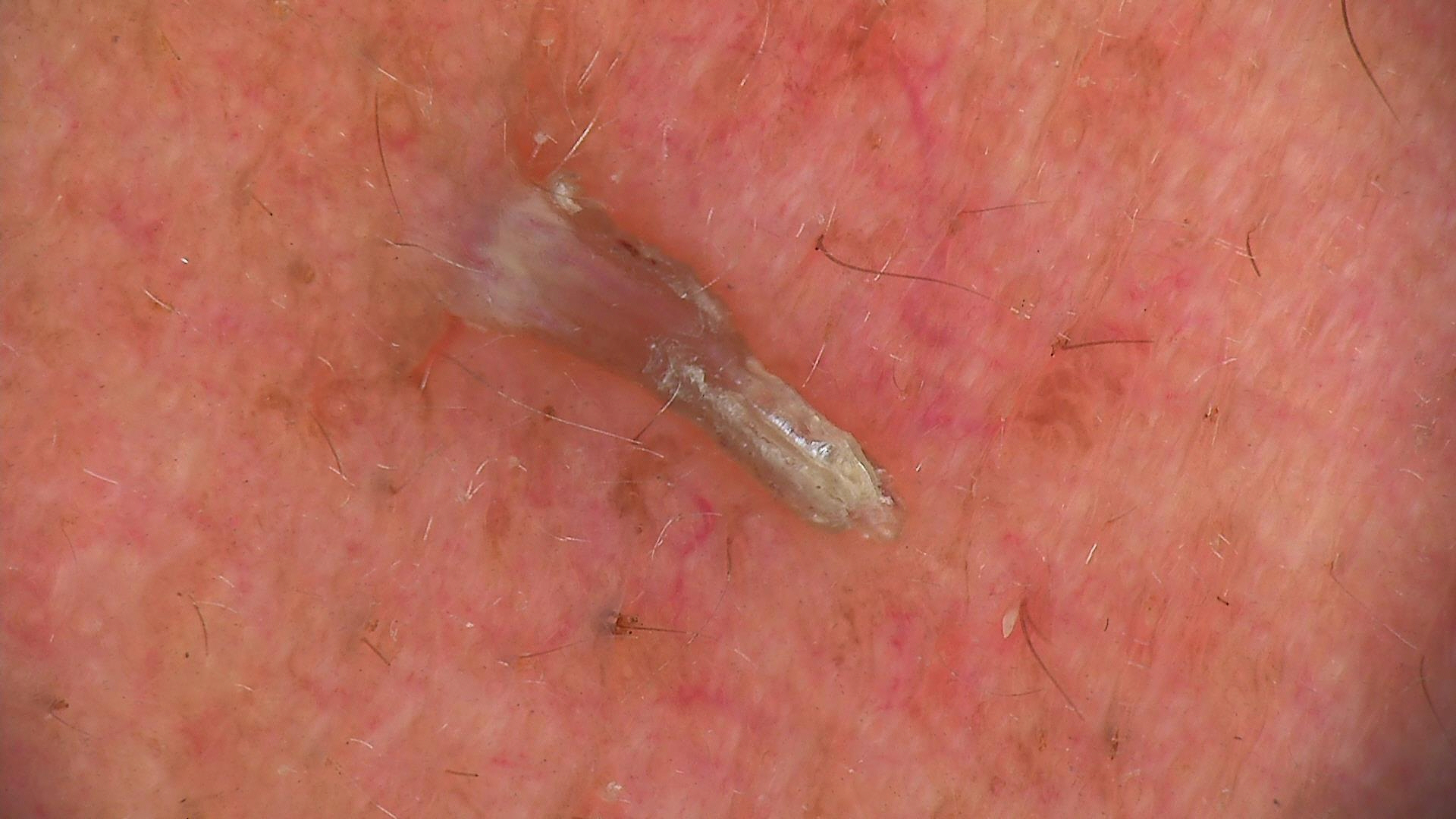{
  "image": "dermoscopy",
  "lesion_type": {
    "main_class": "keratinocytic"
  },
  "diagnosis": {
    "name": "cutaneous horn",
    "code": "ch",
    "malignancy": "malignant",
    "super_class": "non-melanocytic",
    "confirmation": "histopathology"
  }
}